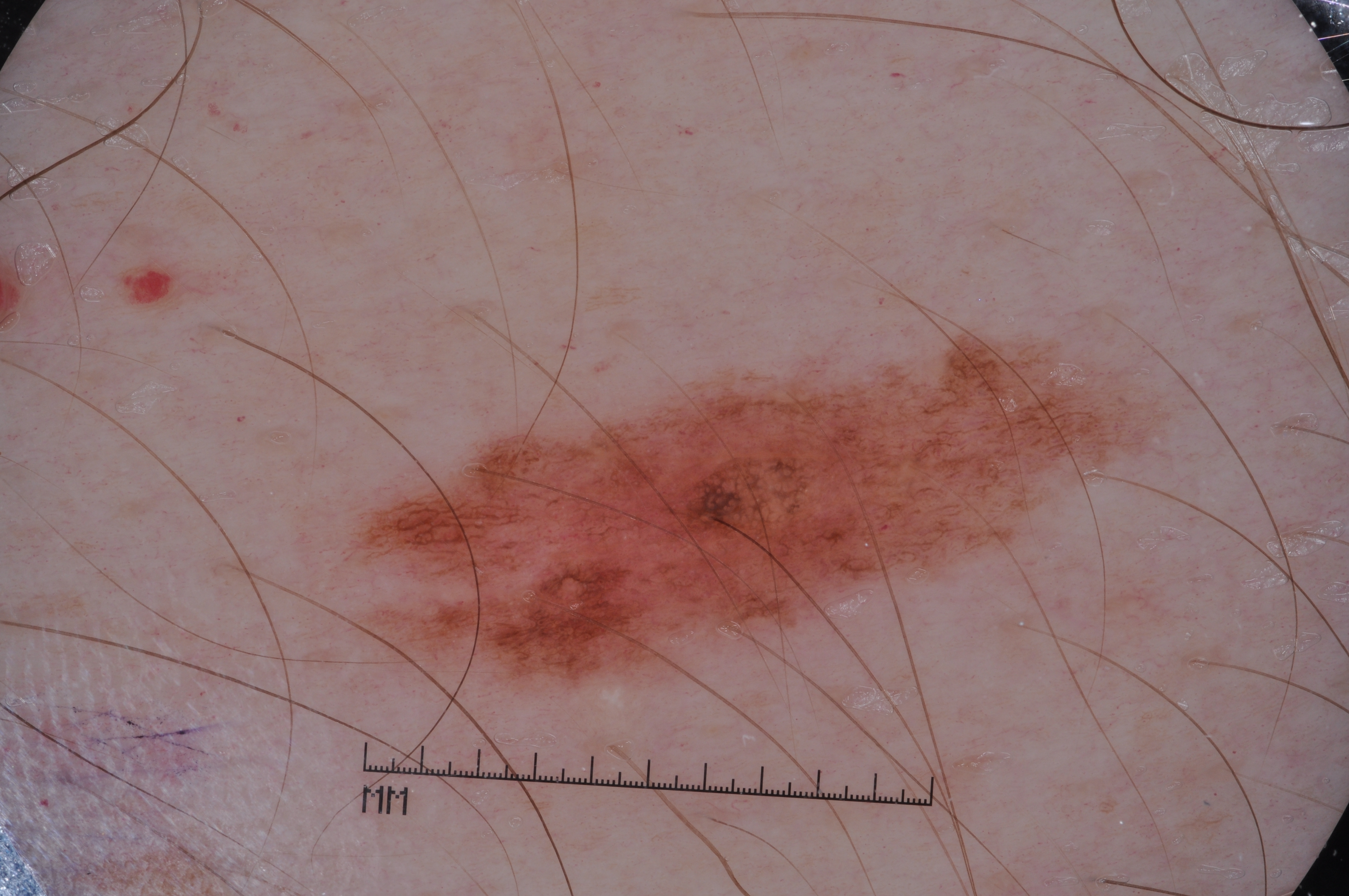The subject is a male in their mid-50s. A dermoscopic close-up of a skin lesion. With coordinates (x1, y1, x2, y2), lesion location: [358, 337, 1138, 686]. Dermoscopic review identifies pigment network and milia-like cysts; no streaks or negative network. Diagnosed as a melanocytic nevus.